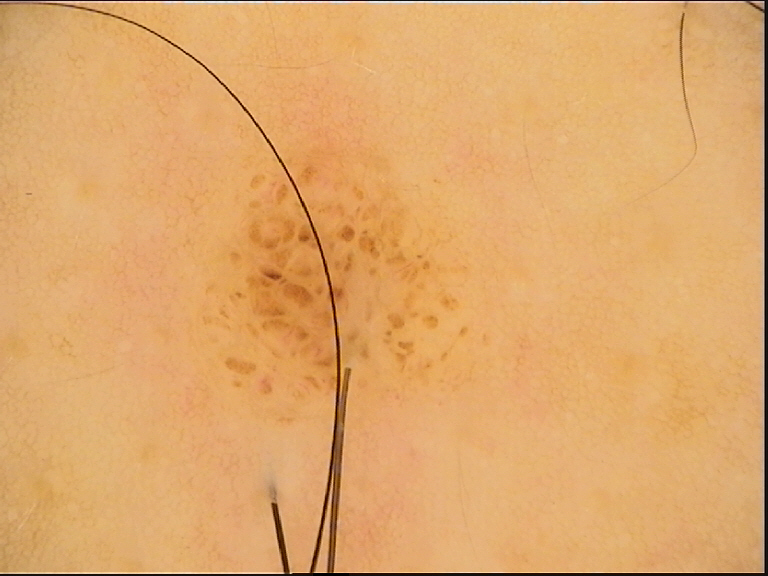label = compound nevus (expert consensus).